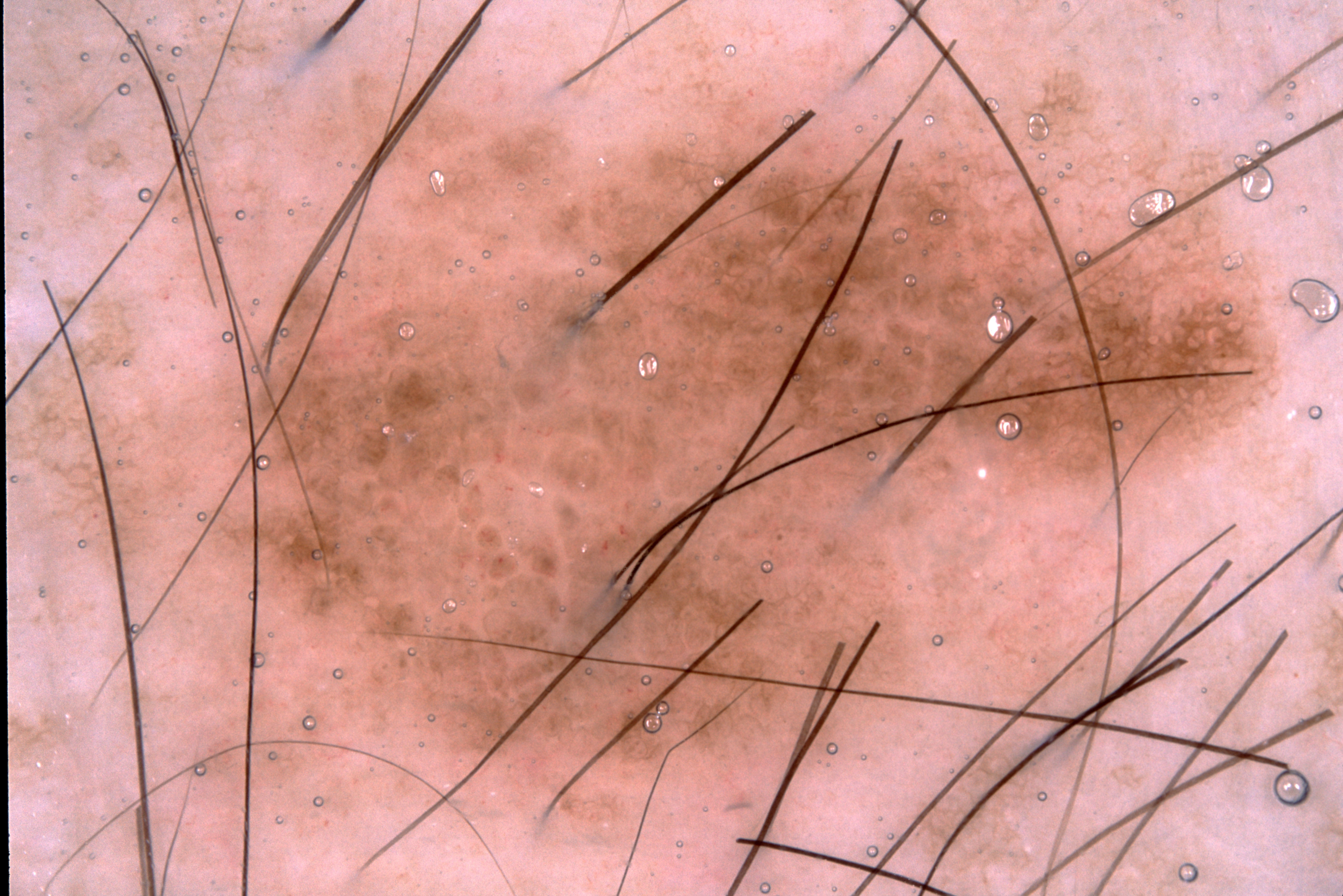imaging: dermoscopy
lesion location: reaches across the whole image
diagnostic label: a melanocytic nevus